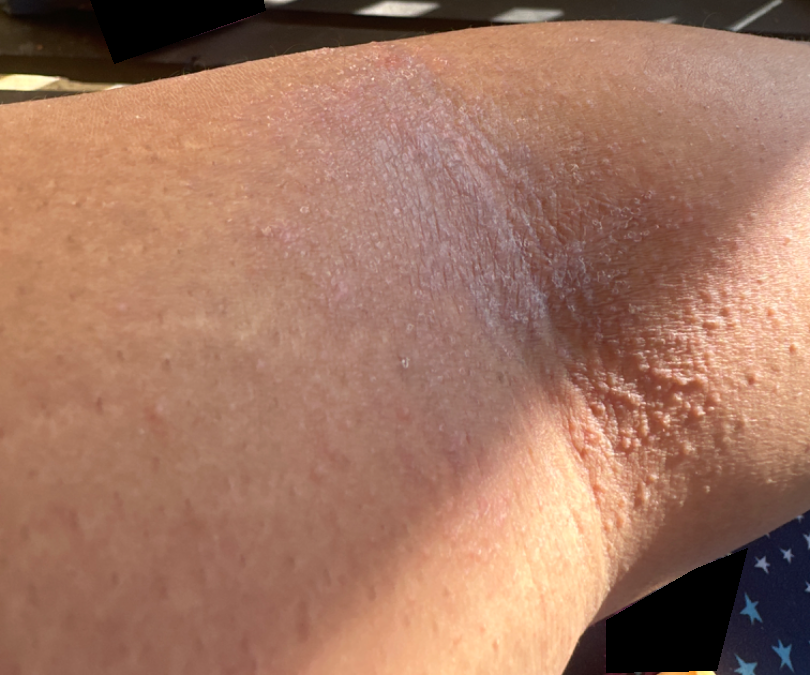This is a close-up image. Reviewed remotely by one dermatologist: most consistent with Eczema.